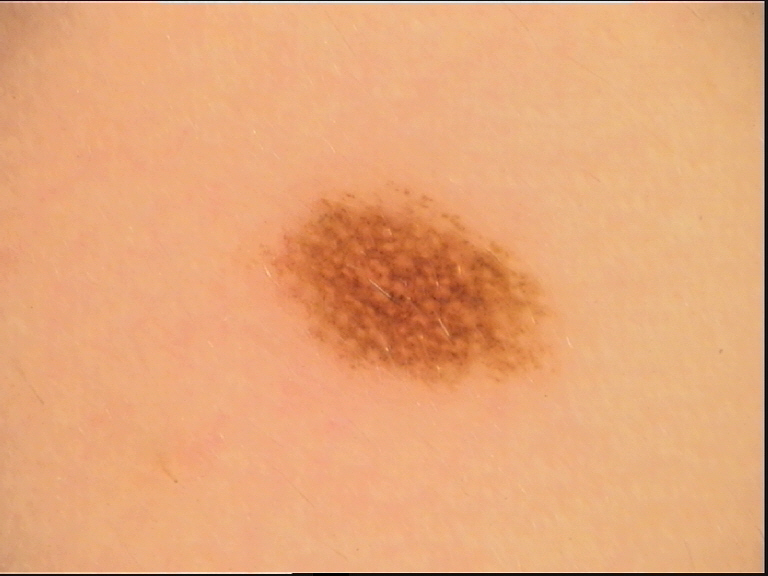A dermoscopic photograph of a skin lesion.
Diagnosed as a dysplastic compound nevus.